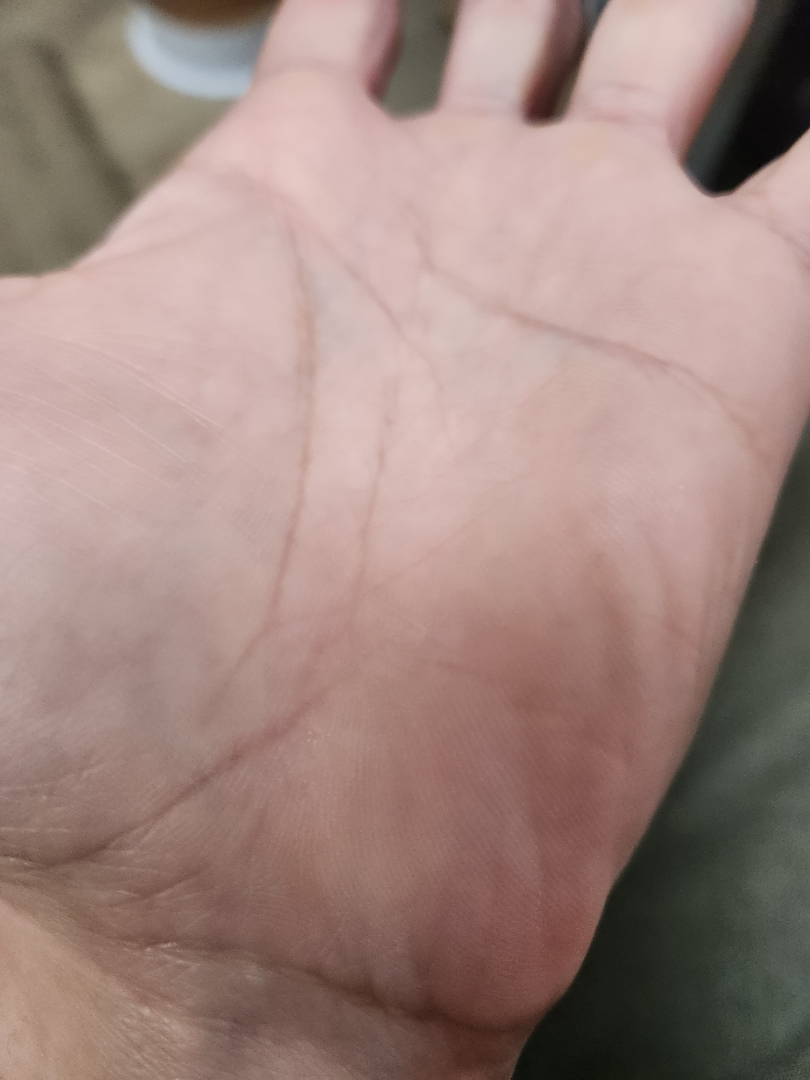On teledermatology review: hyperlinear palm and Eczema were each considered, in no particular order.